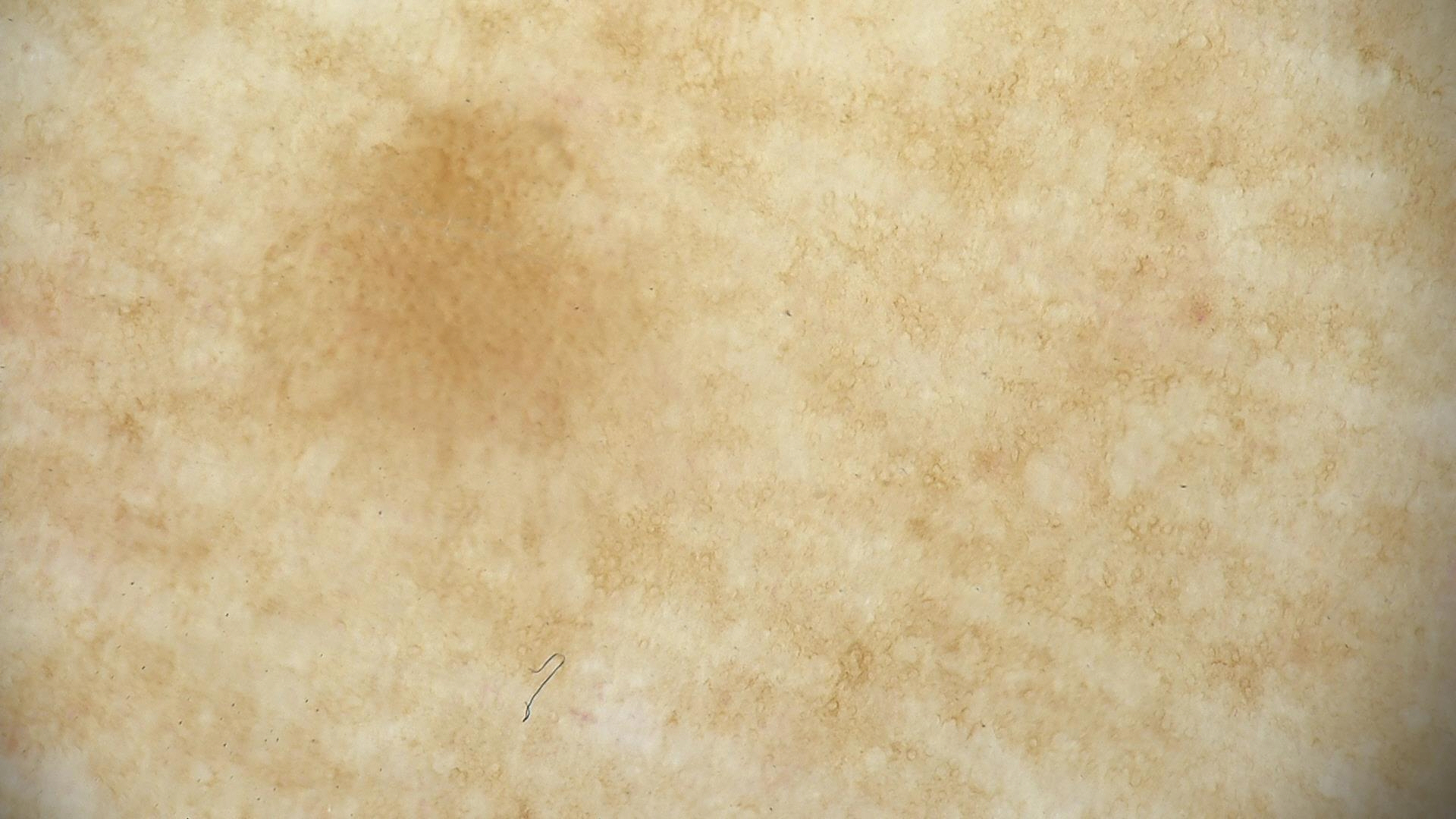{
  "diagnosis": {
    "name": "seborrheic keratosis",
    "code": "sk",
    "malignancy": "benign",
    "super_class": "non-melanocytic",
    "confirmation": "expert consensus"
  }
}